The affected area is the top or side of the foot, palm and back of the hand. The photograph was taken at an angle:
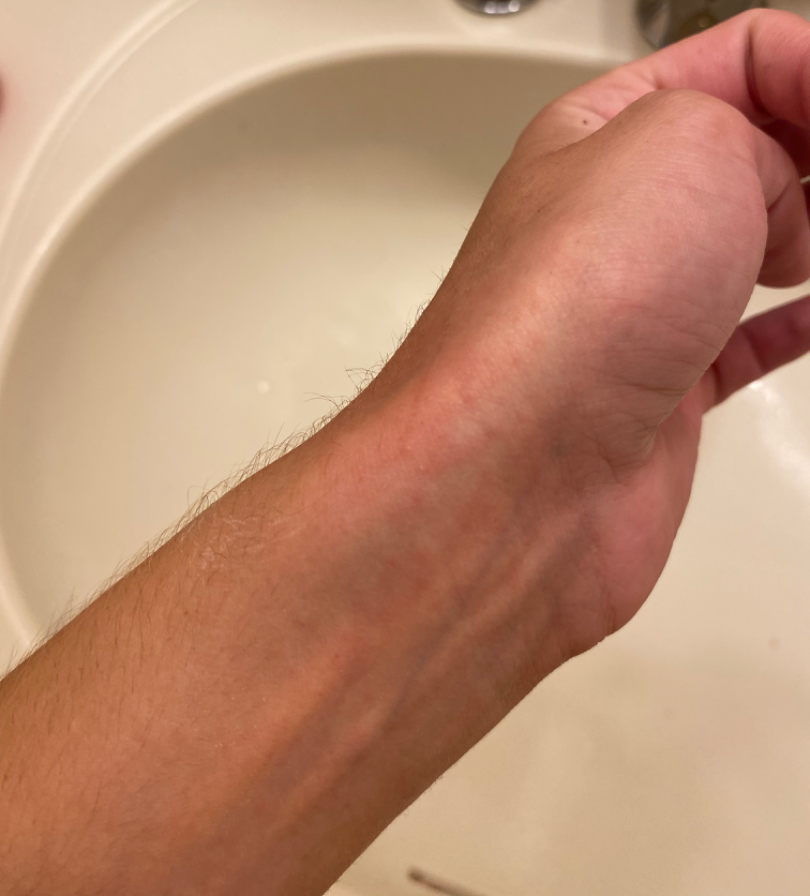Diagnostic features were not clearly distinguishable in this photograph.